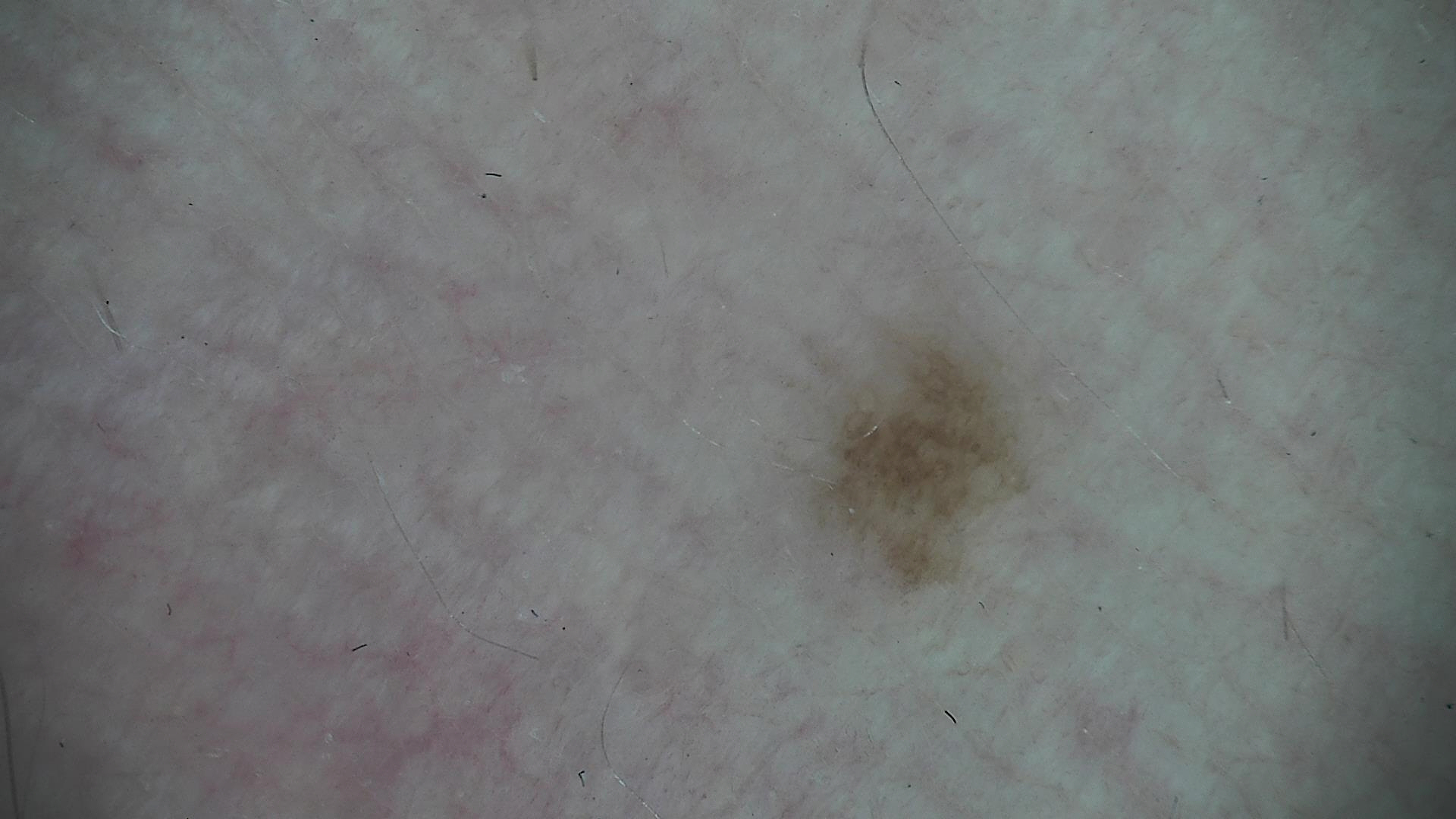A skin lesion imaged with a dermatoscope. Classified as a benign lesion — a dysplastic junctional nevus.